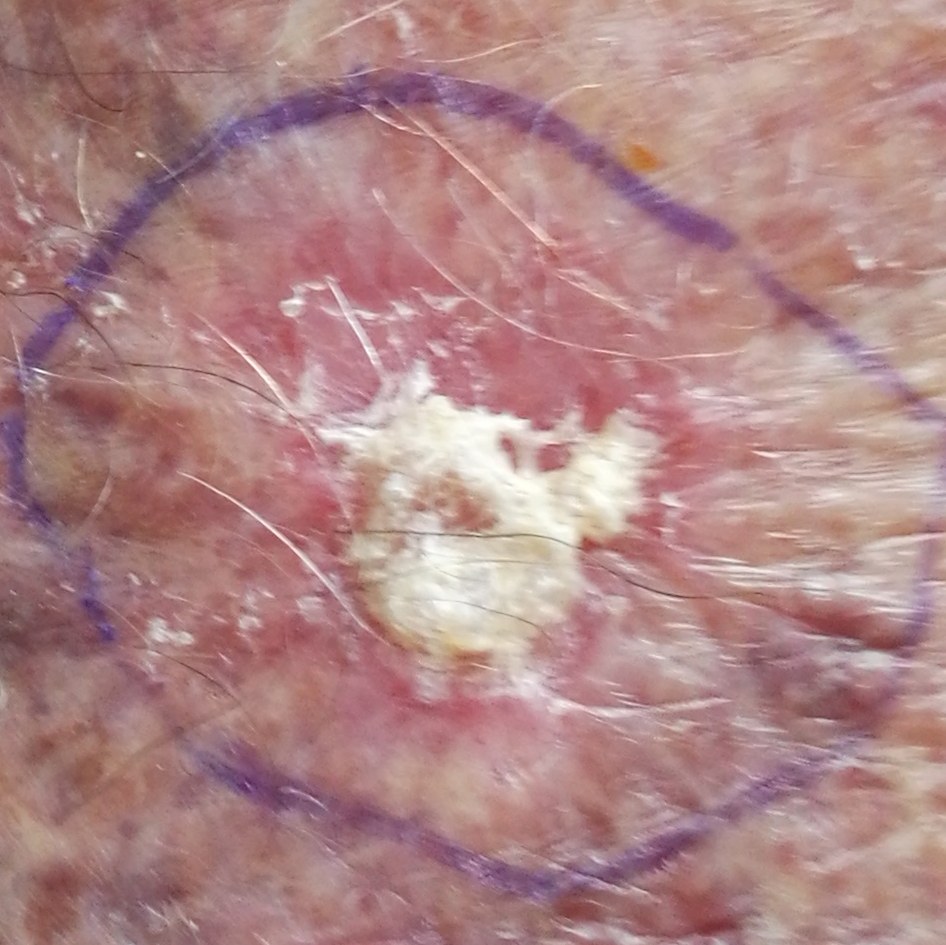skin type: II | modality: clinical photo | subject: female, age 77 | site: a forearm | diameter: 7 × 4 mm | patient-reported symptoms: itching | diagnostic label: actinic keratosis (biopsy-proven).